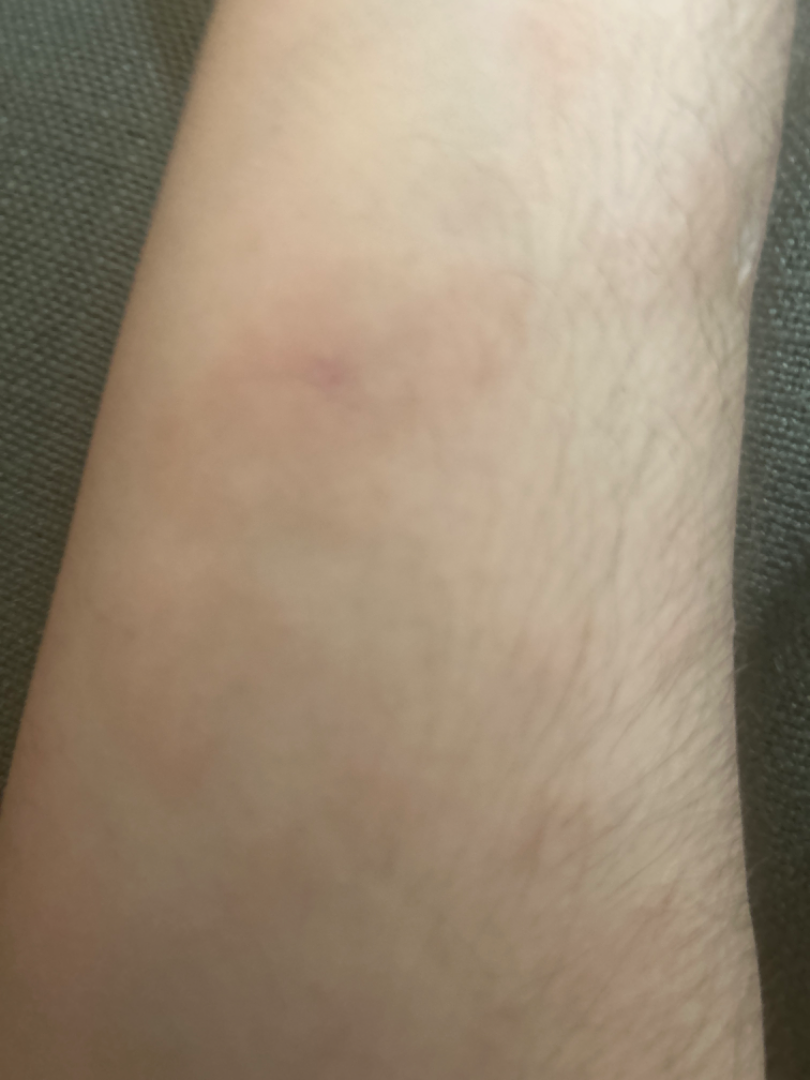Clinical context: The photograph is a close-up of the affected area. The patient is a male aged 40–49. The patient notes the lesion is flat. The lesion involves the arm, front of the torso, head or neck, back of the torso and back of the hand. The patient did not report lesion symptoms. Reported duration is one to four weeks. Self-categorized by the patient as a rash. Skin tone: Fitzpatrick II; human graders estimated MST 2.